The patient is a male approximately 80 years of age, a dermoscopic view of a skin lesion: 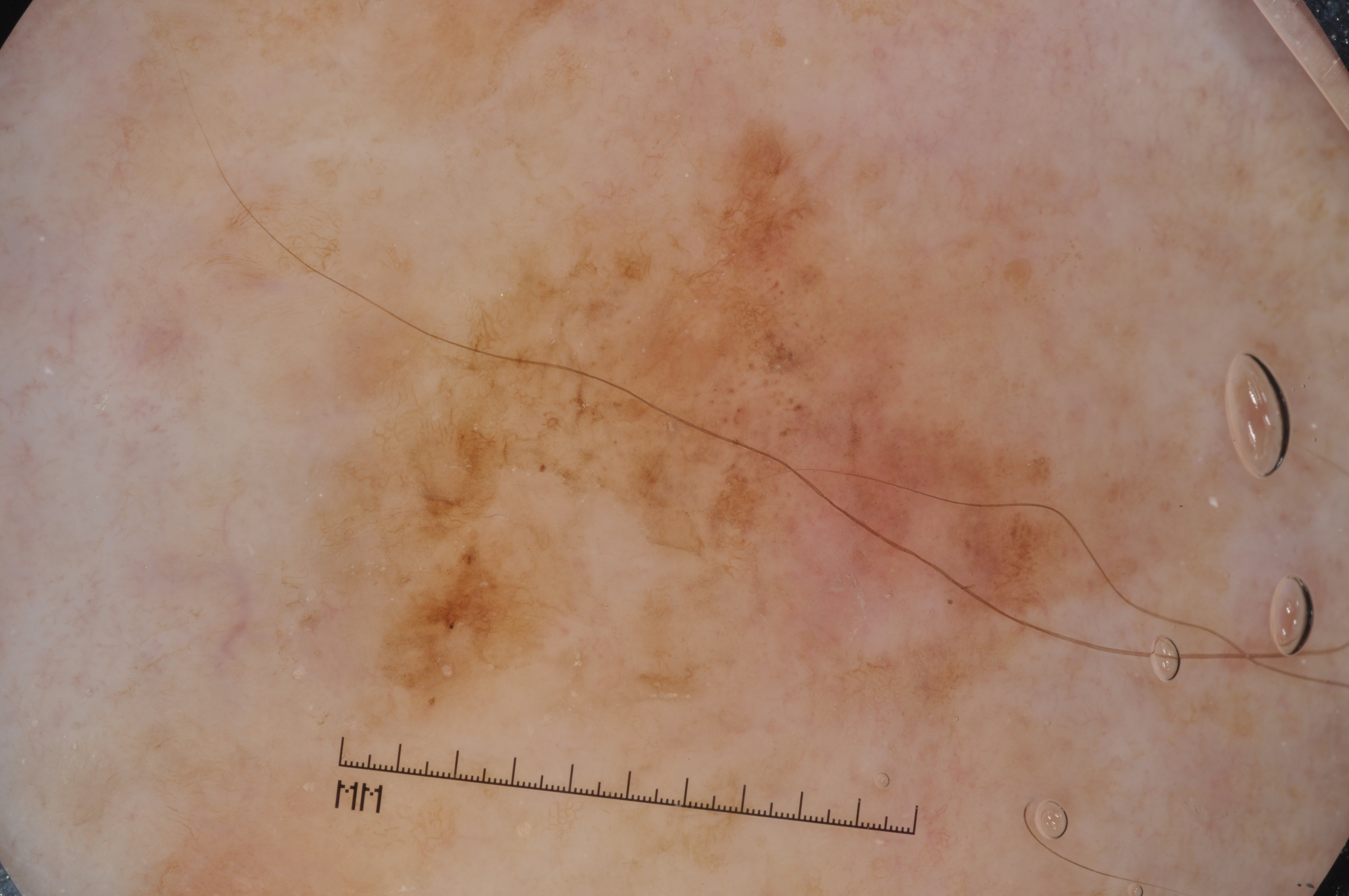Image and clinical context:
Dermoscopic assessment notes milia-like cysts and pigment network; no negative network or streaks. The lesion takes up a large portion of the image. In (x1, y1, x2, y2) order, the lesion is located at bbox(279, 82, 1218, 744).
Conclusion:
The biopsy diagnosis was a melanoma.